The photograph was taken at an angle · located on the front of the torso · the lesion is described as raised or bumpy · the subject is 18–29, female · the patient reports itching · the patient described the issue as a rash · Fitzpatrick phototype II; non-clinician graders estimated Monk skin tone scale 2 or 3 (two reviewer pools) · present for about one day — 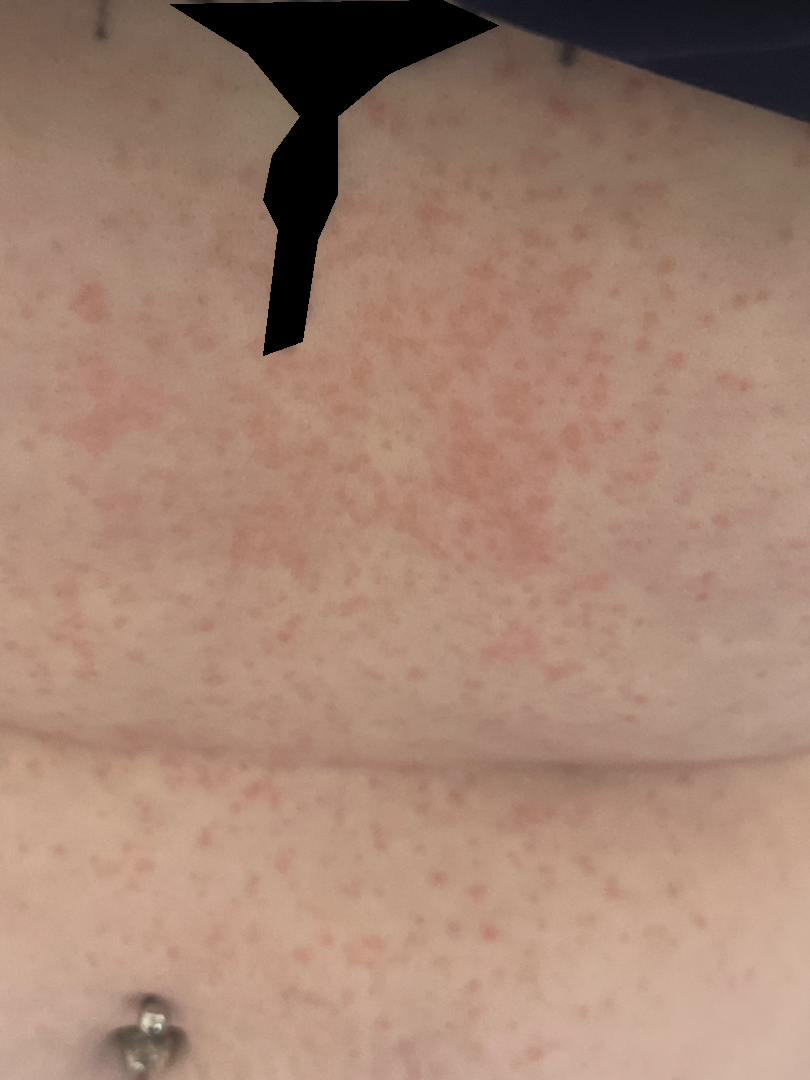On teledermatology review: the differential is split between Drug Rash and Viral Exanthem.